A clinical photo of a skin lesion taken with a smartphone. A female patient 59 years old. By history, prior skin cancer (patient or family), prior malignancy (patient or family), and pesticide exposure.
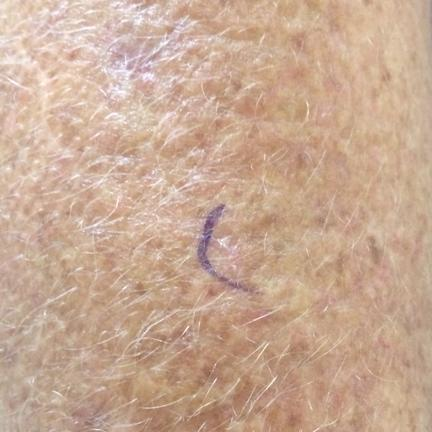The lesion is on a forearm. Measuring about 15 × 13 mm. Per patient report, the lesion itches, but has not bled. The diagnostic impression was a lesion of indeterminate malignant potential — an actinic keratosis.